On a questionnaire the patient reported no family history of skin cancer and no prior organ transplant; a macroscopic clinical photograph of a skin lesion; collected as part of a research study, without a referral diagnosis; a male patient 83 years of age; the patient says their skin reddens with sun exposure — 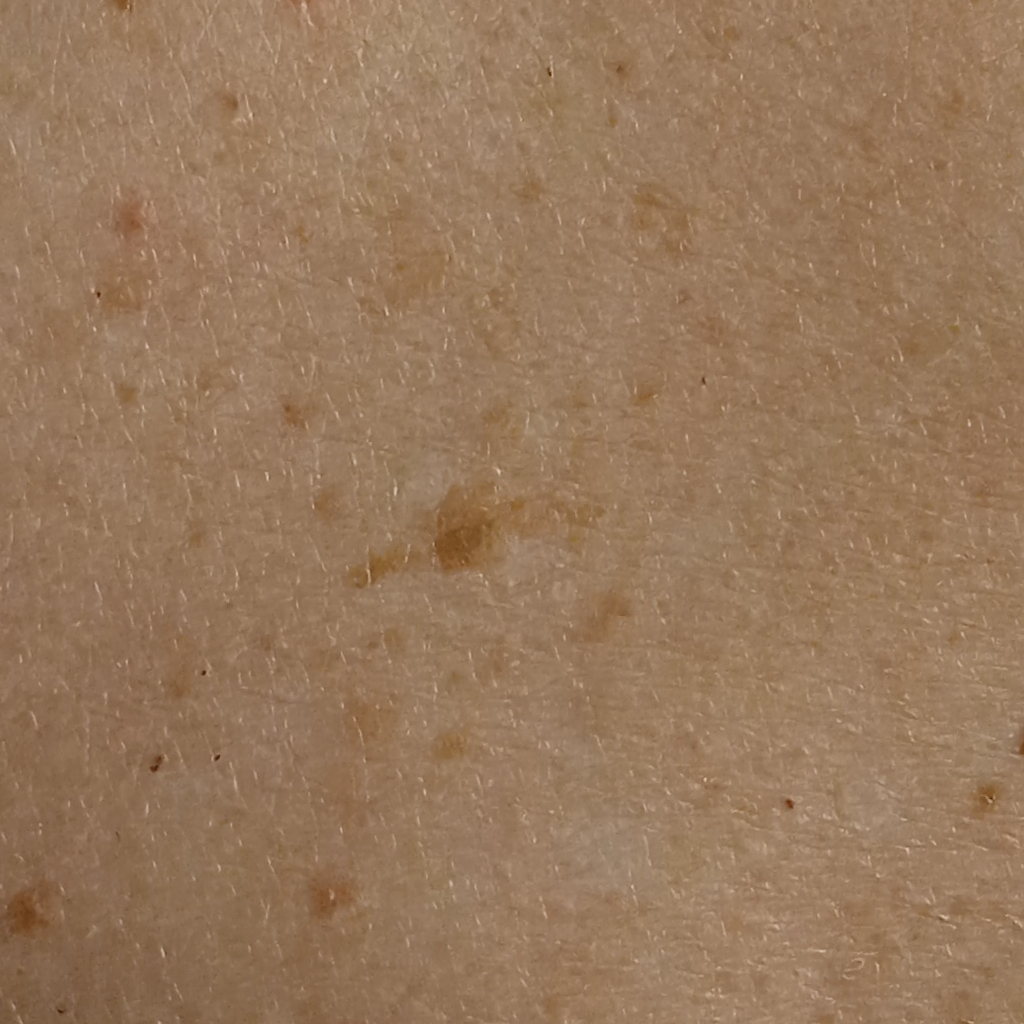Q: What is the anatomic site?
A: the back
Q: How large is the lesion?
A: 16.4 mm
Q: What was the diagnosis?
A: seborrheic keratosis (dermatologist consensus)